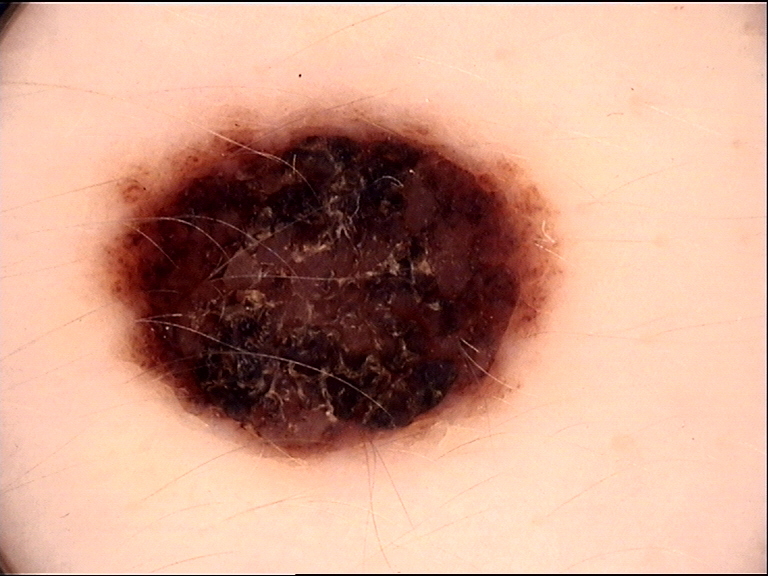The diagnostic label was a benign lesion — a congenital dysplastic compound nevus.